A dermoscopic close-up of a skin lesion: 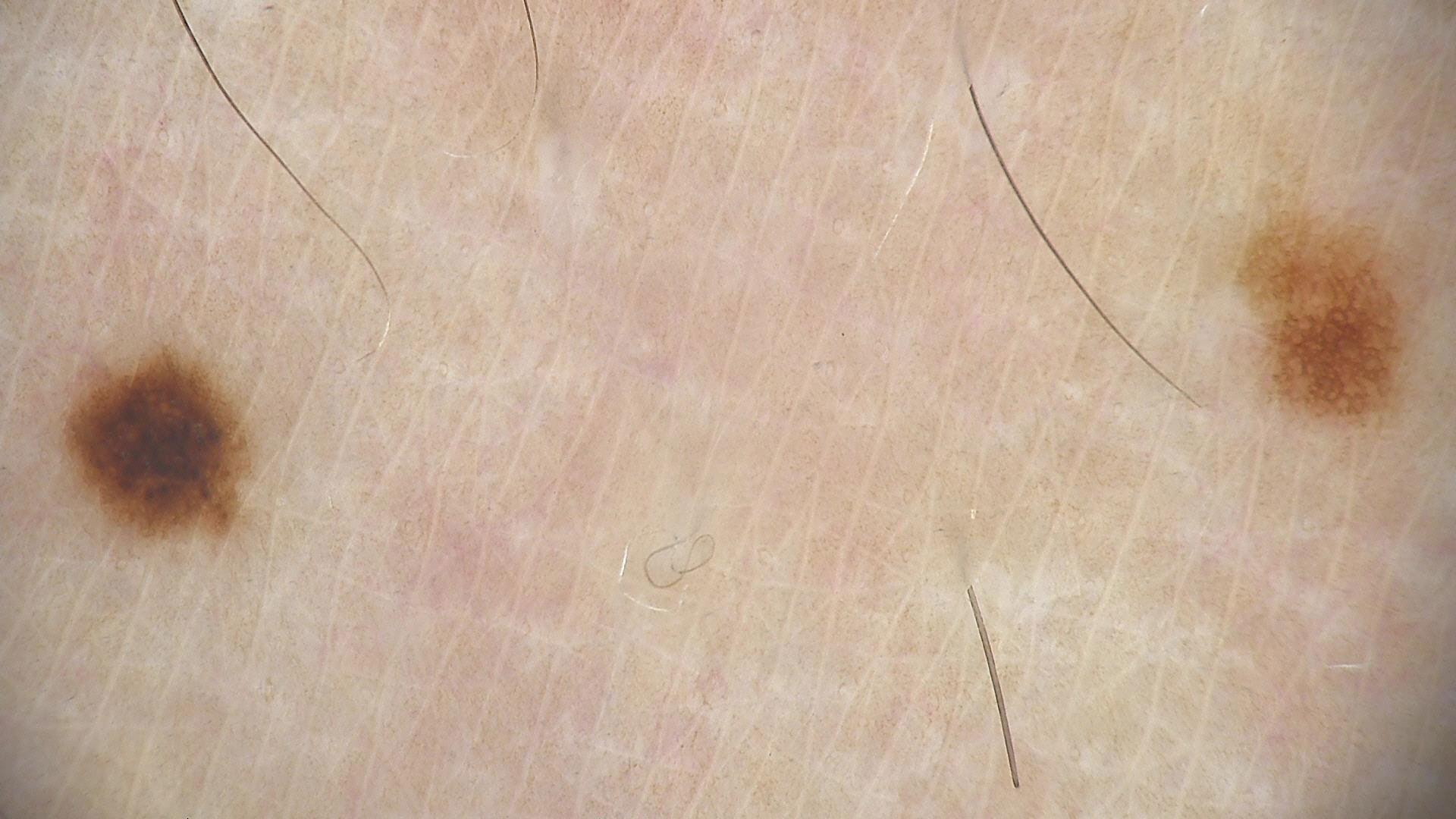class = dysplastic junctional nevus (expert consensus).